A dermoscopy image of a single skin lesion: 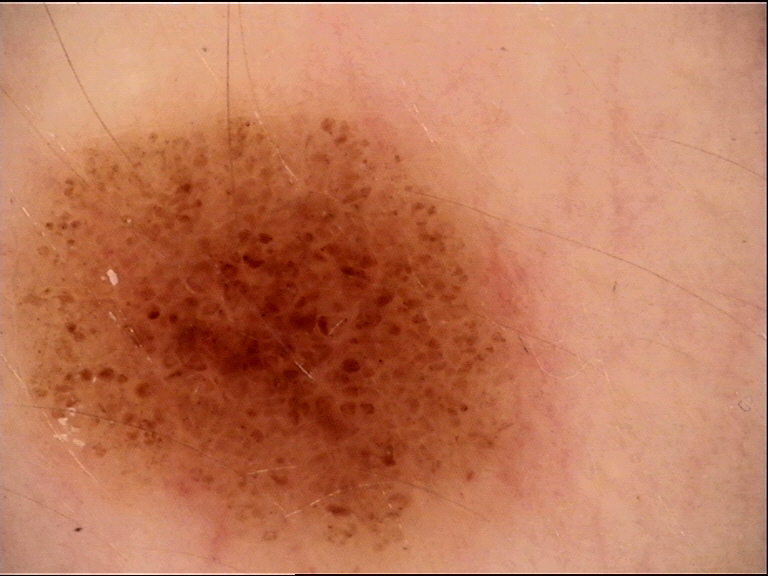<case>
  <lesion_type>
    <main_class>banal</main_class>
    <pattern>junctional</pattern>
  </lesion_type>
  <diagnosis>
    <name>junctional nevus</name>
    <code>jb</code>
    <malignancy>benign</malignancy>
    <super_class>melanocytic</super_class>
    <confirmation>expert consensus</confirmation>
  </diagnosis>
</case>